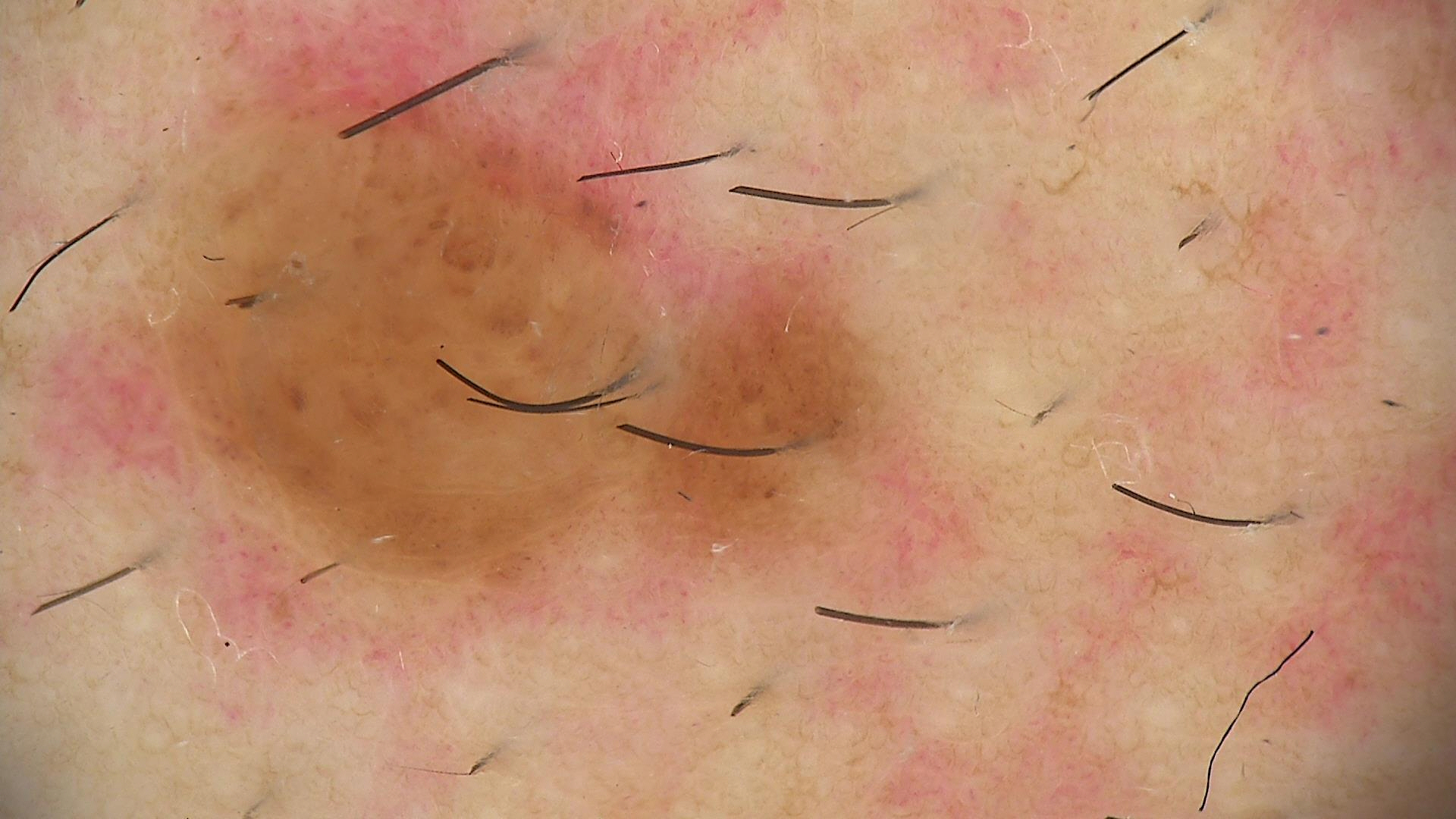Findings:
The morphology is that of a banal lesion.
Conclusion:
The diagnostic label was a compound nevus.